Female contributor, age 30–39 · no associated systemic symptoms reported · texture is reported as raised or bumpy and fluid-filled · this is a close-up image · the condition has been present for one to three months · the patient described the issue as a rash.
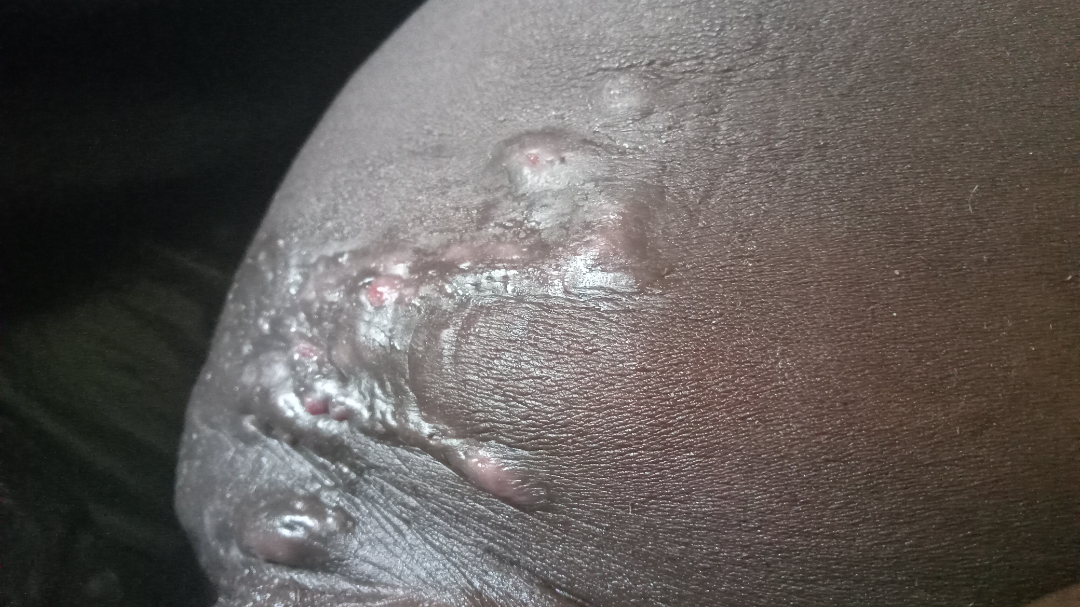The skin findings could not be characterized from the image.